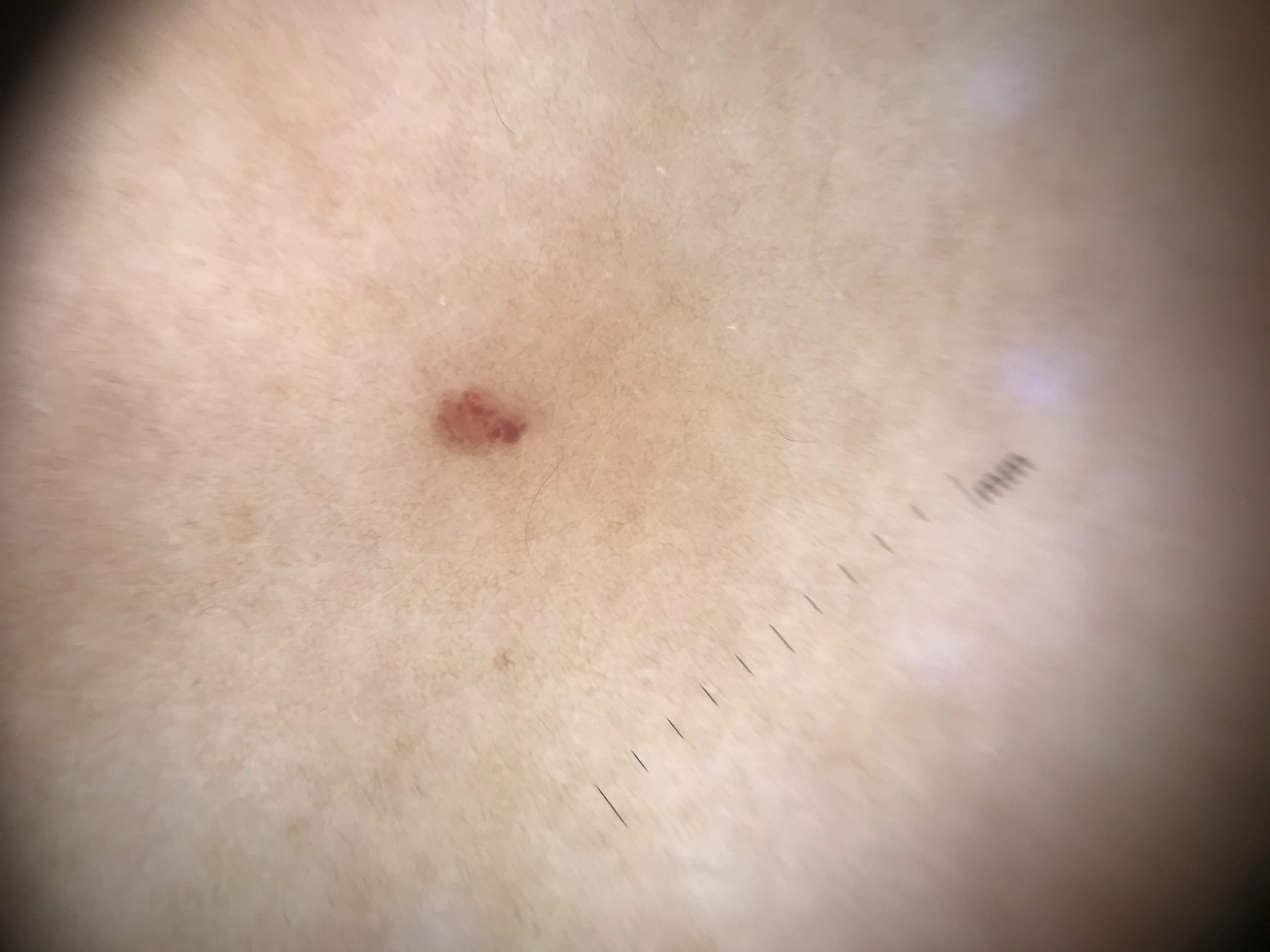Findings: A dermoscopic photograph of a skin lesion. This is a vascular lesion. Conclusion: The diagnosis was a benign lesion — a hemangioma.